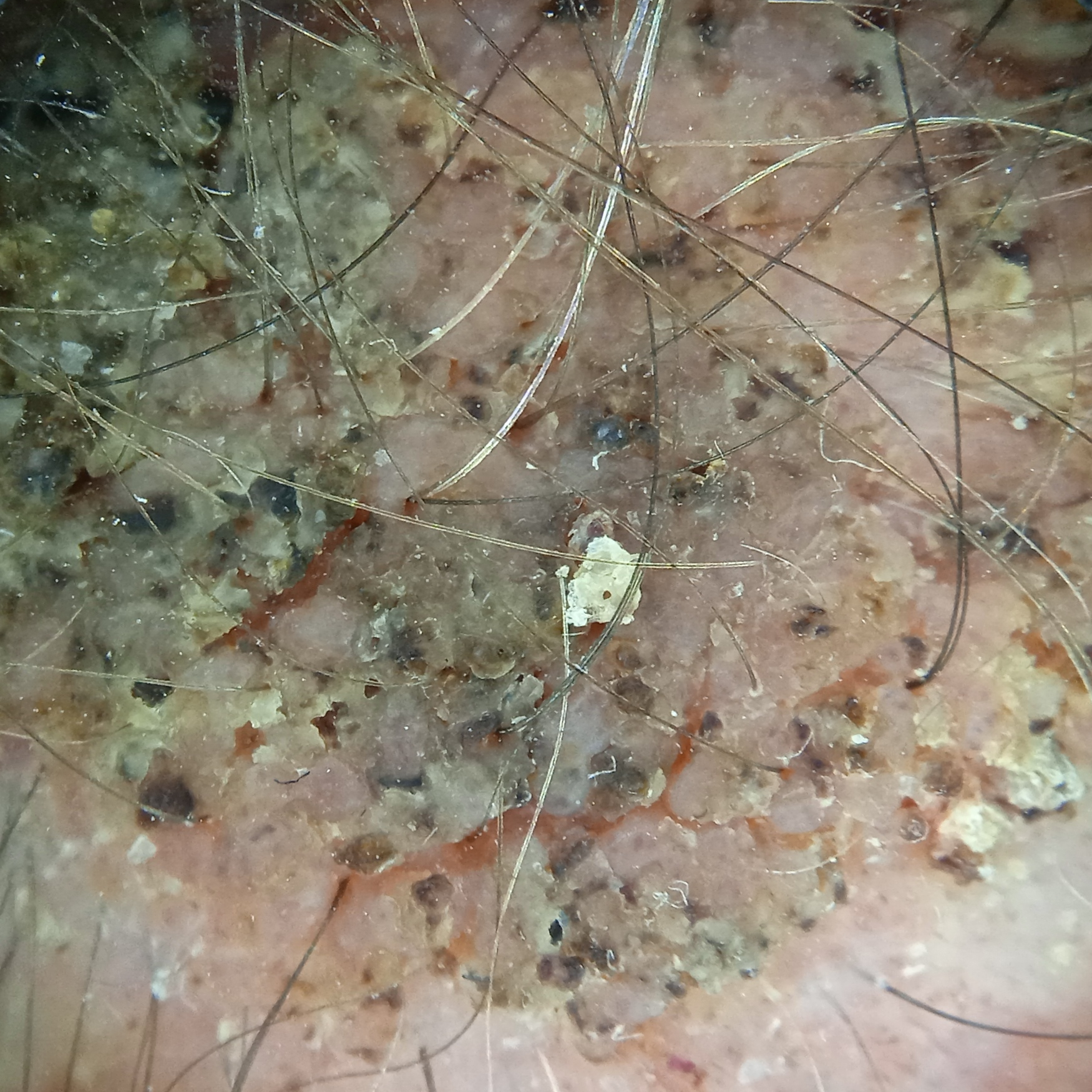{
  "patient": {
    "age": 72,
    "sex": "male"
  },
  "risk_factors": {
    "negative": [
      "no sunbed use"
    ]
  },
  "referral": "research study (no referral diagnosis)",
  "sun_reaction": "skin tans without first burning",
  "mole_burden": "a moderate number of melanocytic nevi",
  "lesion_location": "the head",
  "lesion_size": {
    "diameter_mm": 19.2
  },
  "diagnosis": {
    "name": "seborrheic keratosis",
    "malignancy": "benign",
    "unanimous": false,
    "certainty": "good"
  }
}